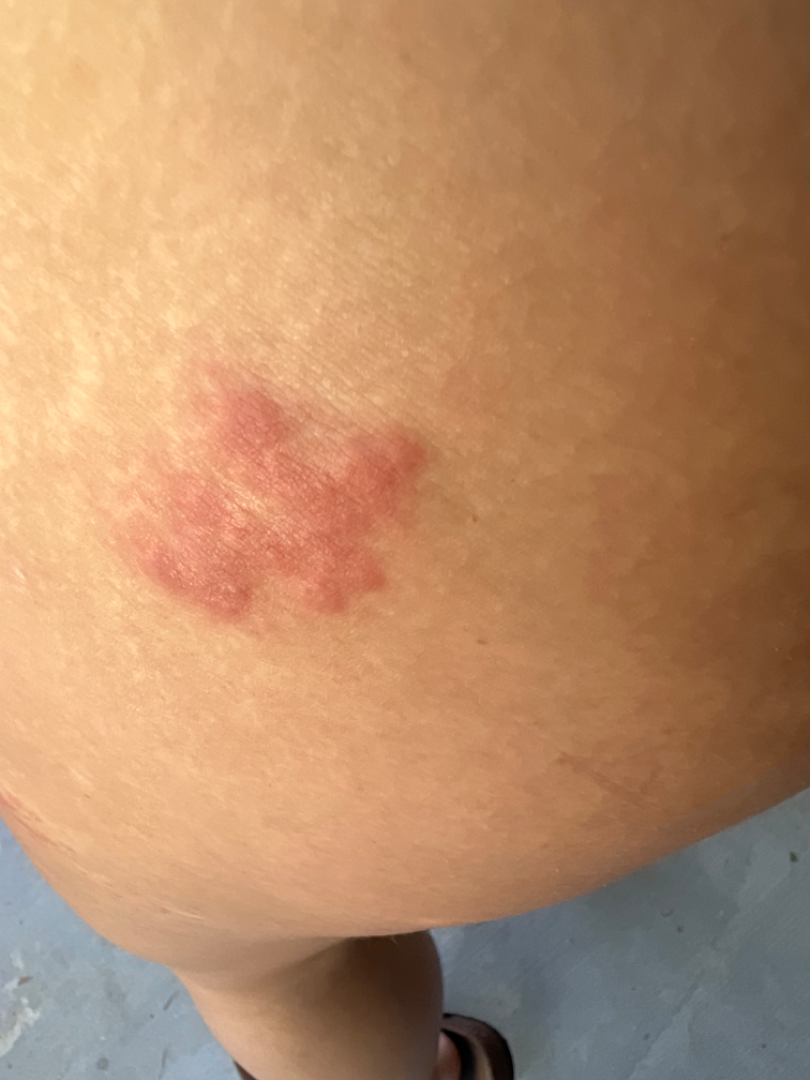| key | value |
|---|---|
| assessment | not assessable |
| patient's own categorization | skin that appeared healthy to them |
| view | at an angle |
| duration | about one day |
| site | leg |